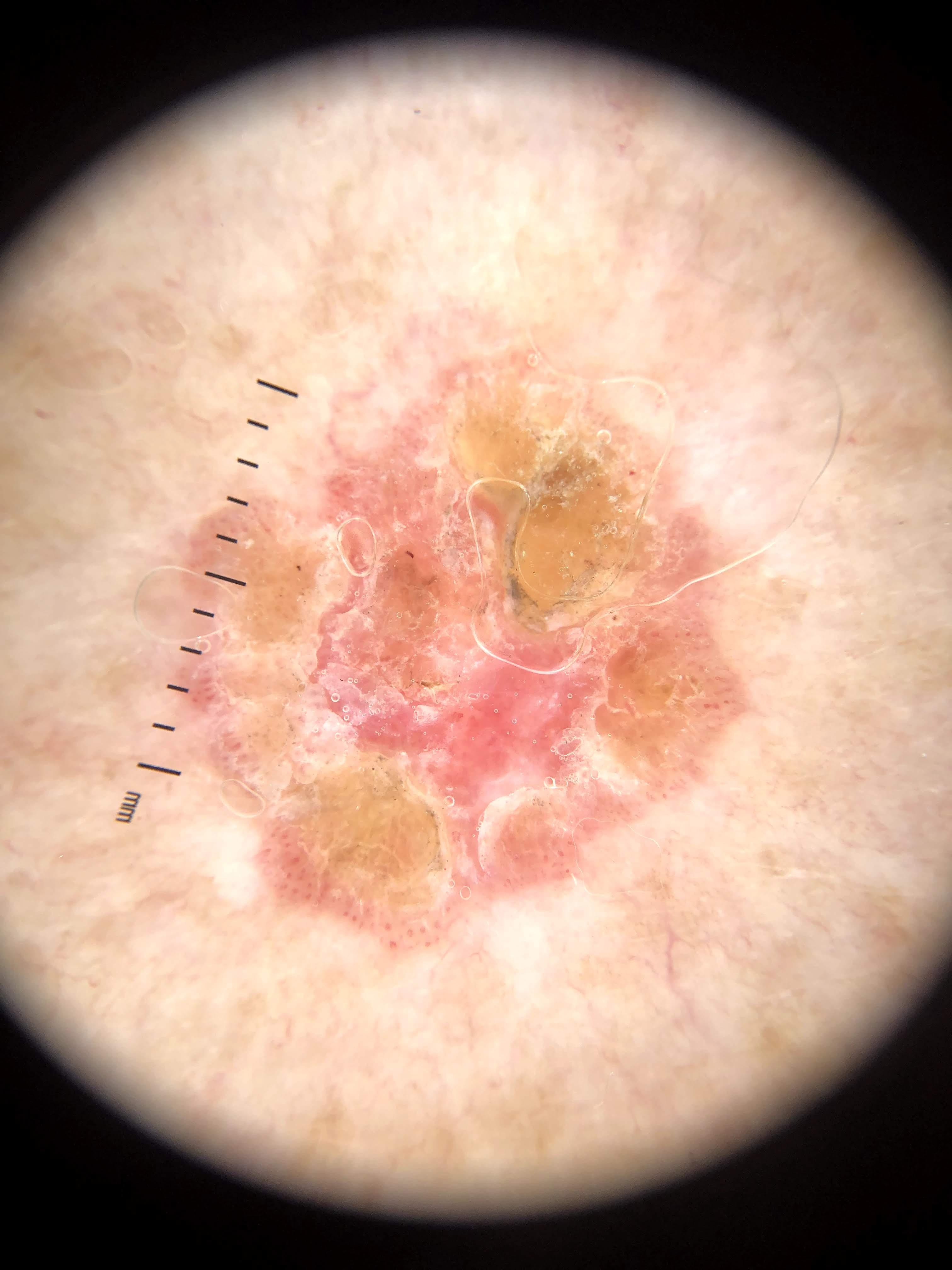The patient is Fitzpatrick III.
A female patient in their mid-80s or older.
A dermatoscopic image of a skin lesion.
The biopsy diagnosis was a squamous cell carcinoma.